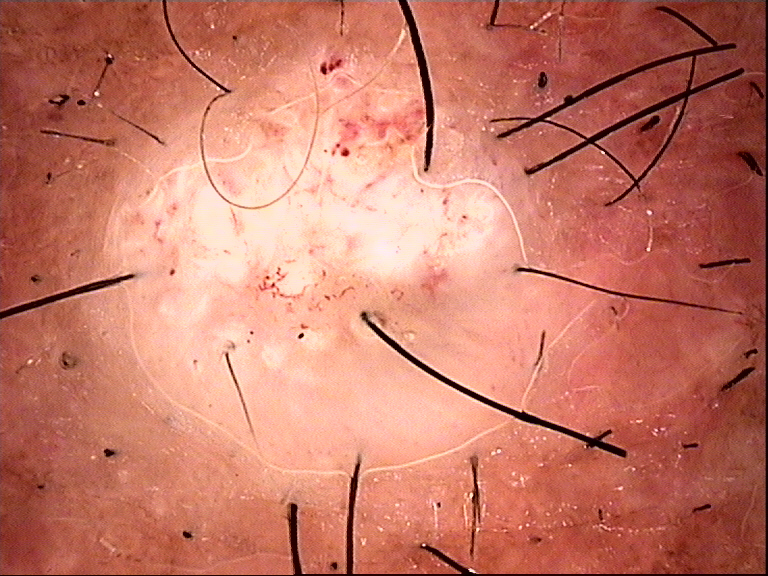Summary:
A dermatoscopic image of a skin lesion. The architecture is that of a keratinocytic lesion.
Diagnosis:
Histopathologically confirmed as a squamous cell carcinoma.